Texture is reported as fluid-filled and raised or bumpy · the photograph was taken at a distance · the condition has been present for less than one week · the patient is a male aged 50–59 · reported lesion symptoms include enlargement · located on the leg · the patient described the issue as a rash:
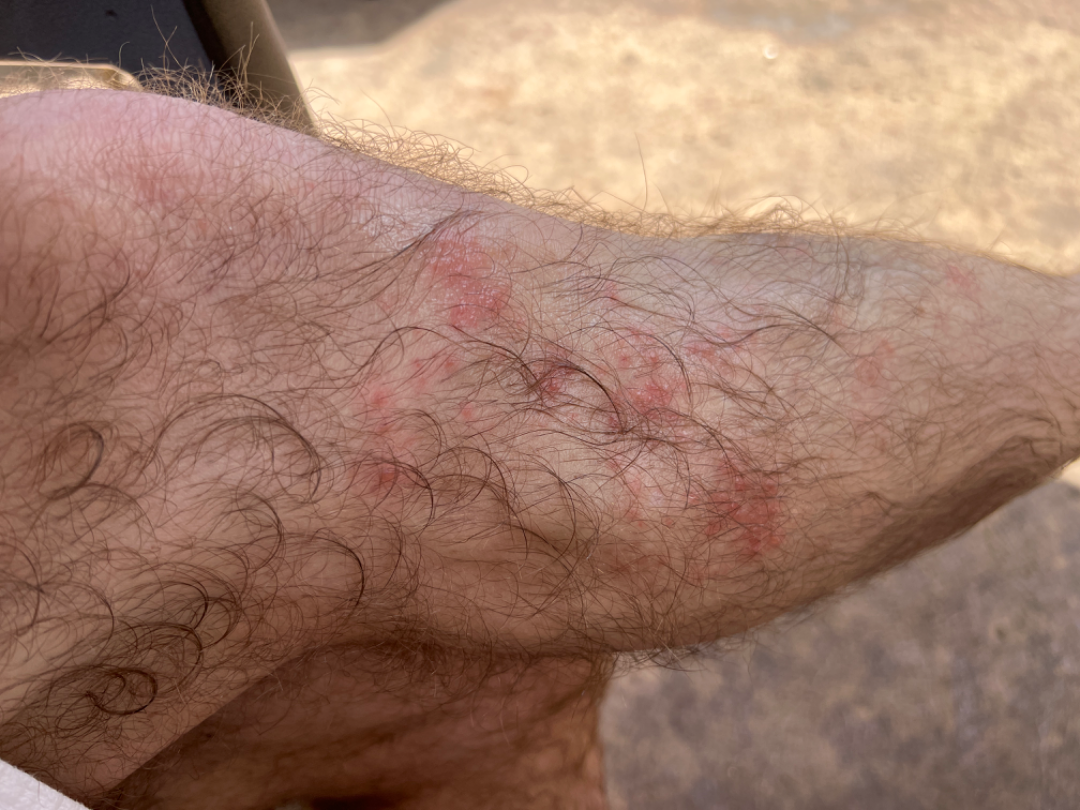assessment: unable to determine.